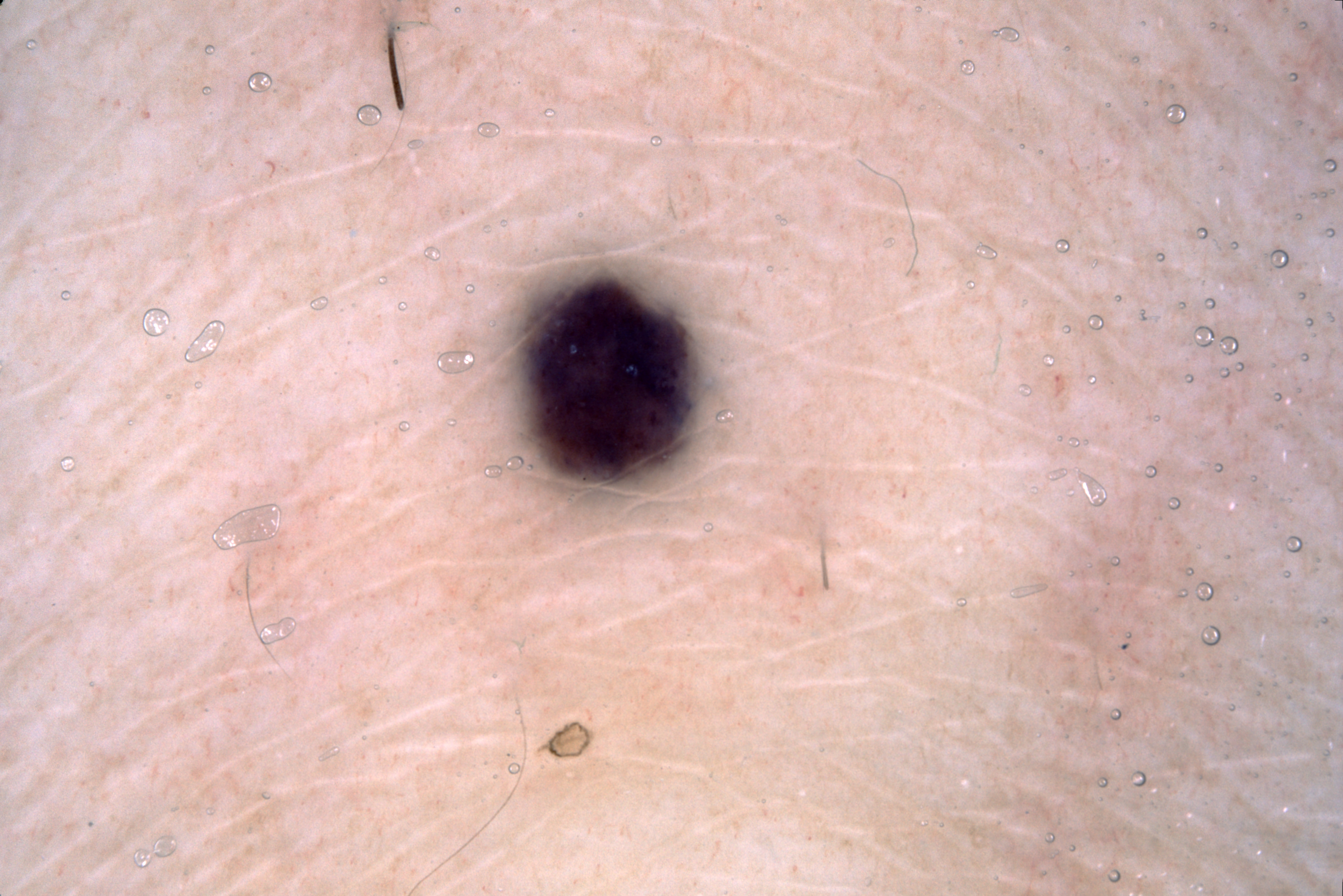{
  "image": {
    "modality": "dermoscopy"
  },
  "lesion_location": {
    "bbox_xyxy": [
      503,
      262,
      716,
      505
    ]
  },
  "diagnosis": {
    "name": "melanocytic nevus",
    "malignancy": "benign",
    "lineage": "melanocytic",
    "provenance": "clinical"
  }
}